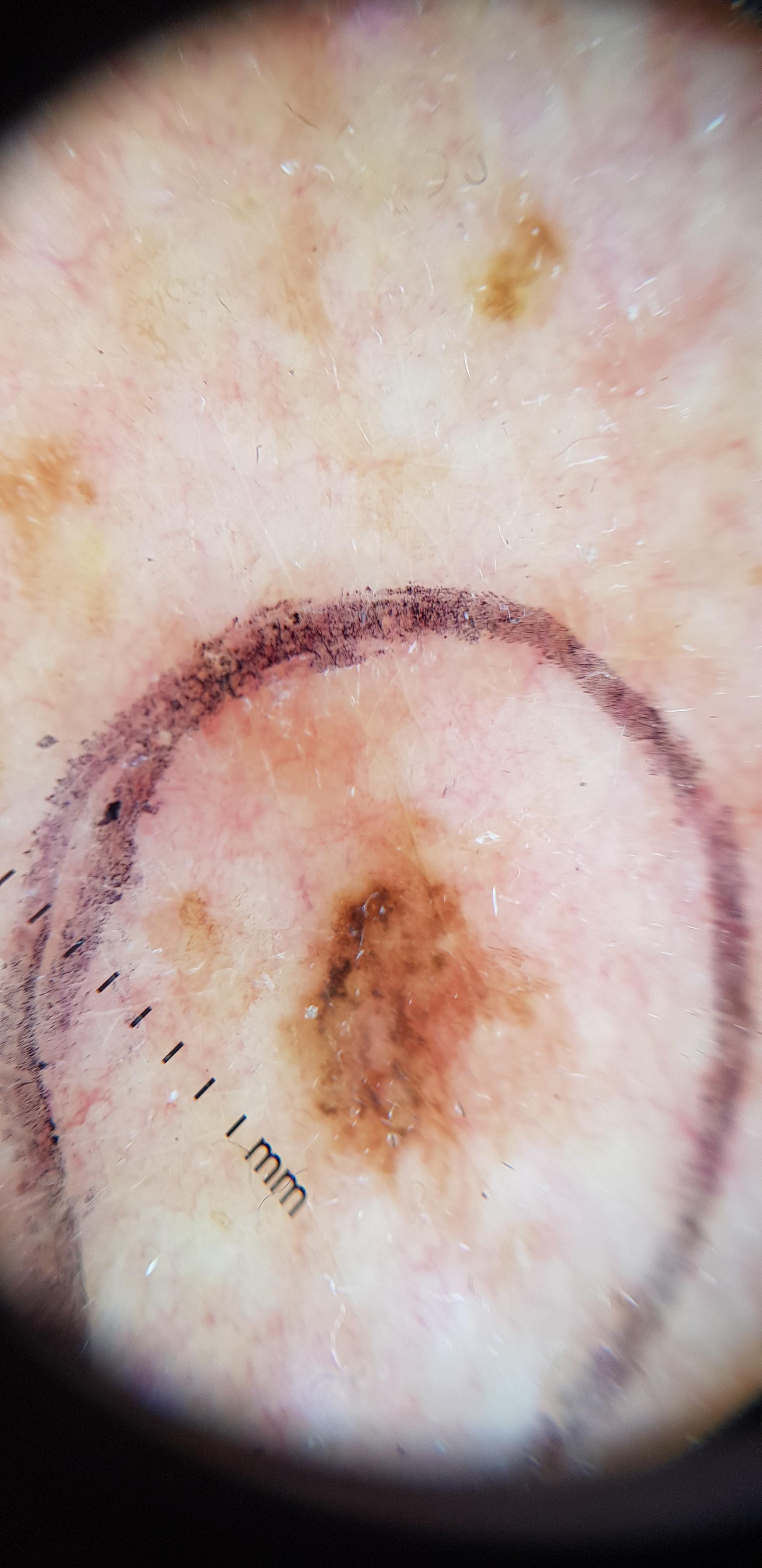The biopsy diagnosis was a melanoma.